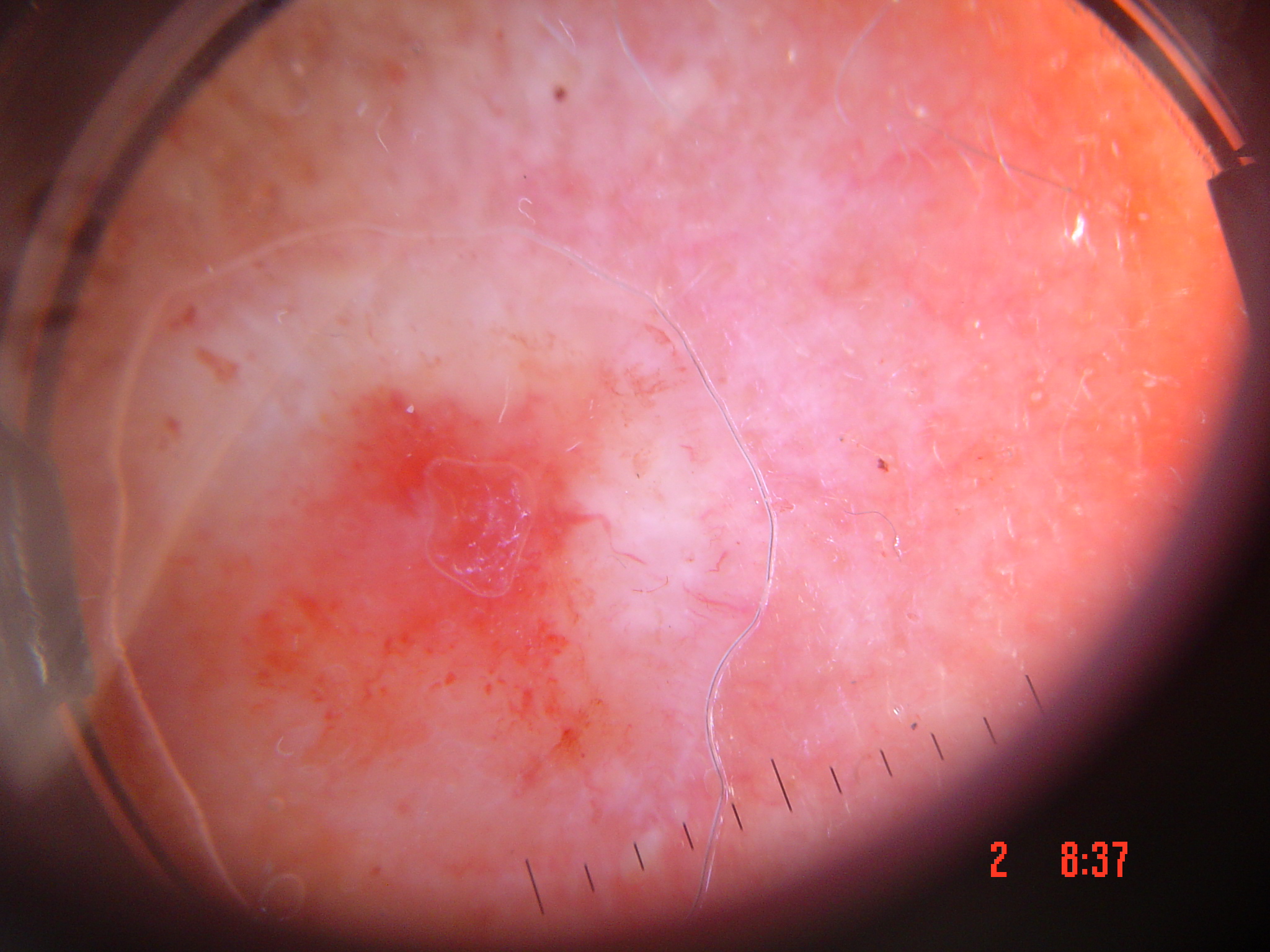diagnostic label=squamous cell carcinoma (biopsy-proven).